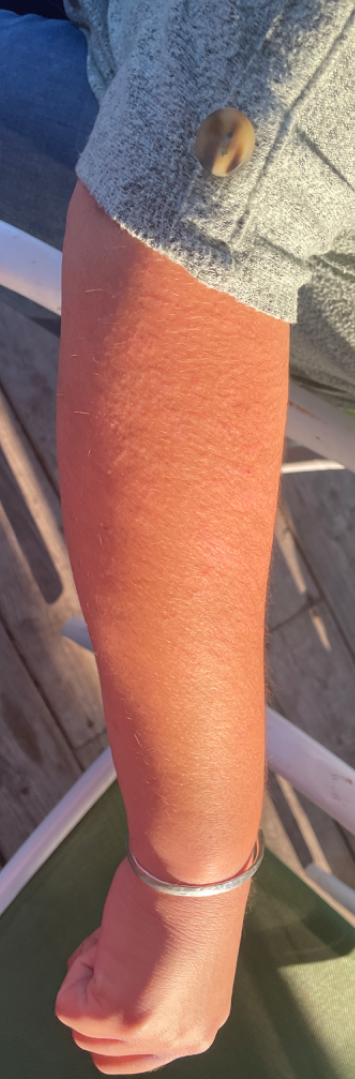Assessment:
The dermatologist could not determine a likely condition from the photograph alone.
Clinical context:
Texture is reported as raised or bumpy. An image taken at a distance. The subject is 30–39, female. The condition has been present for more than one year. The arm and head or neck are involved.